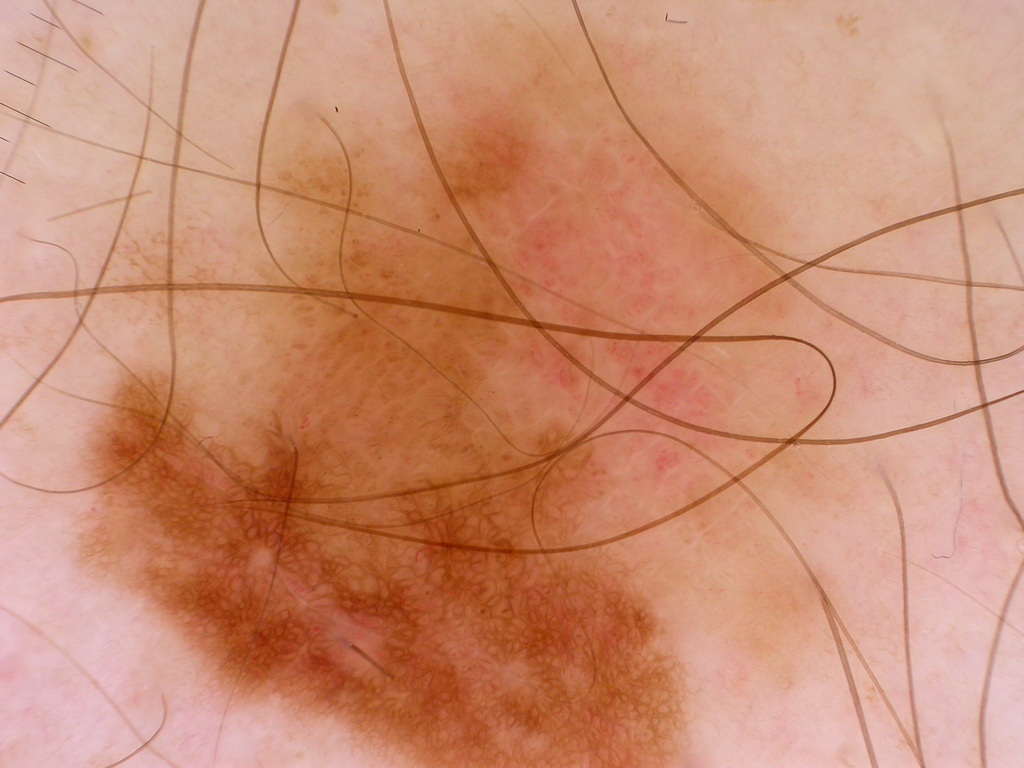• modality: dermoscopy of a skin lesion
• location: [67,1,898,766]
• diagnostic label: a melanoma, a malignancy